The condition has been present for less than one week. The patient notes enlargement, pain, itching and bothersome appearance. This is a close-up image. The patient notes associated fatigue. Fitzpatrick skin type IV.
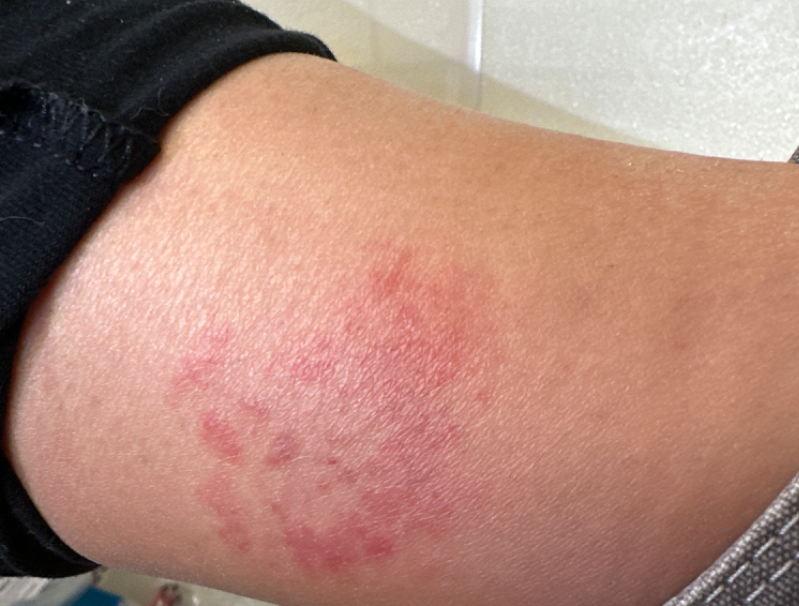On photographic review: most consistent with Irritant Contact Dermatitis; possibly Acute dermatitis, NOS.